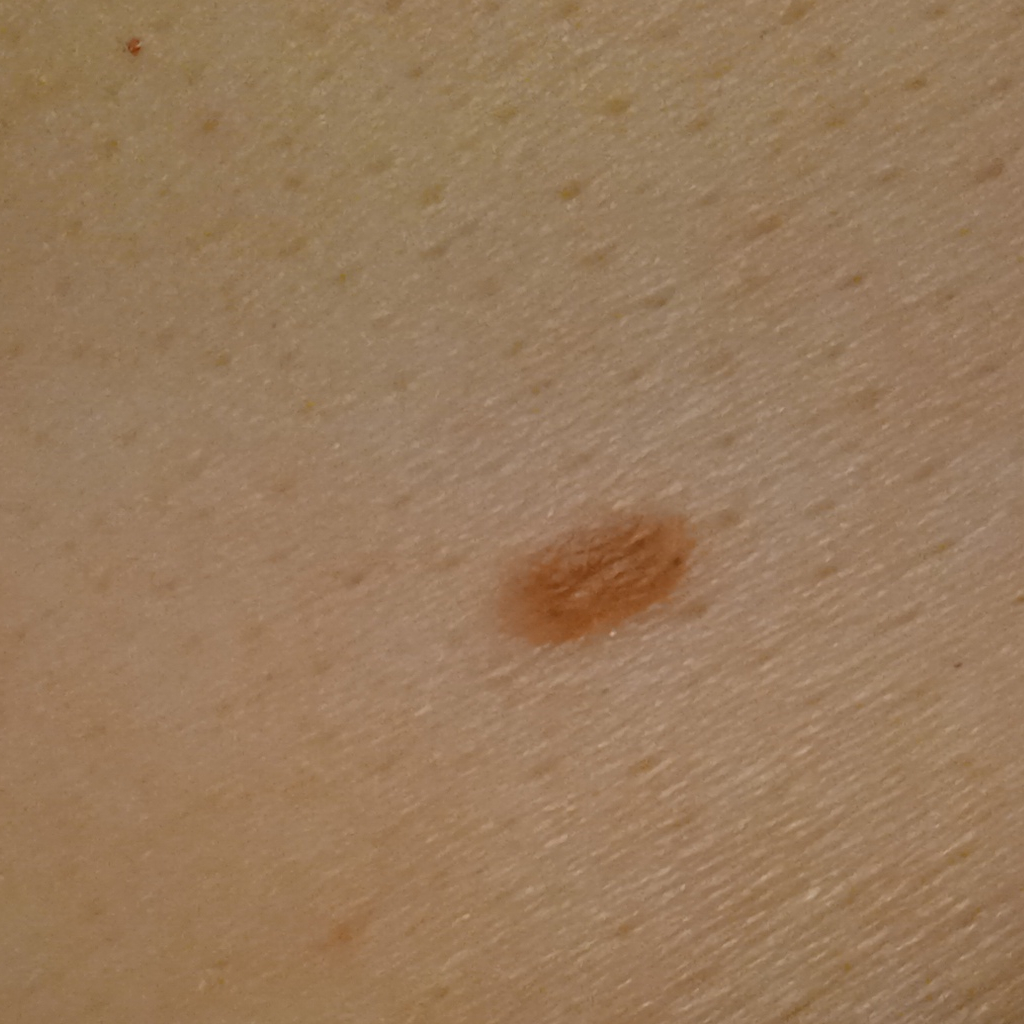A clinical photograph showing a skin lesion.
The patient describes having a moderate number of moles.
The patient says their skin reddens painfully with sun exposure.
A female subject 50 years old.
The lesion is on the torso.
Measuring roughly 4.9 mm.
Dermatologist review favored a melanocytic nevus.